The affected area is the head or neck. Close-up view. Fitzpatrick II.
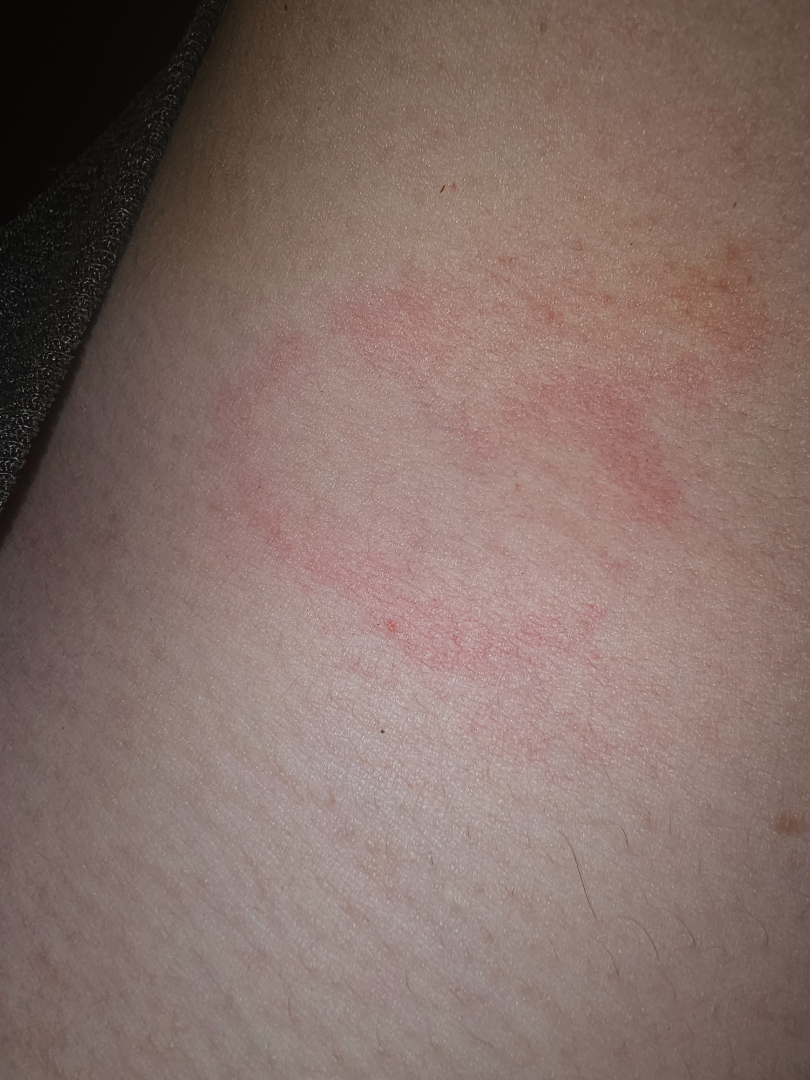* assessment — one reviewing dermatologist: the differential is split between Tinea, Pityriasis rosea and Allergic Contact Dermatitis